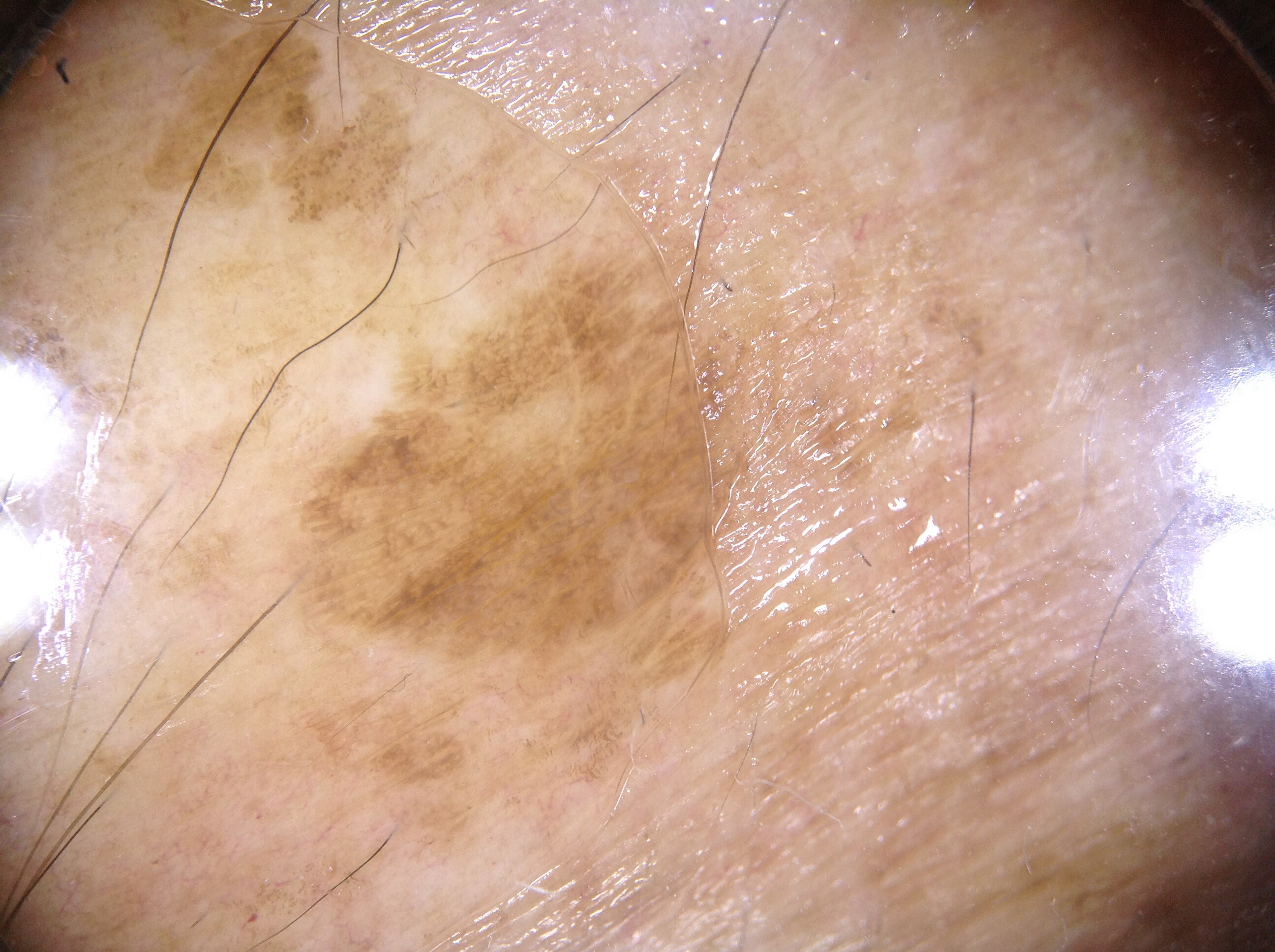A dermoscopic view of a skin lesion. The subject is a male aged around 80. On dermoscopy, the lesion shows no streaks, negative network, milia-like cysts, or pigment network. The lesion's extent is 277 221 776 690. The lesion takes up about 15% of the image. The diagnostic assessment was a seborrheic keratosis.